The patient was assessed as Fitzpatrick skin type III. A clinical close-up photograph of a skin lesion. History notes pesticide exposure, prior skin cancer (patient or family), prior malignancy (patient or family), and no alcohol use:
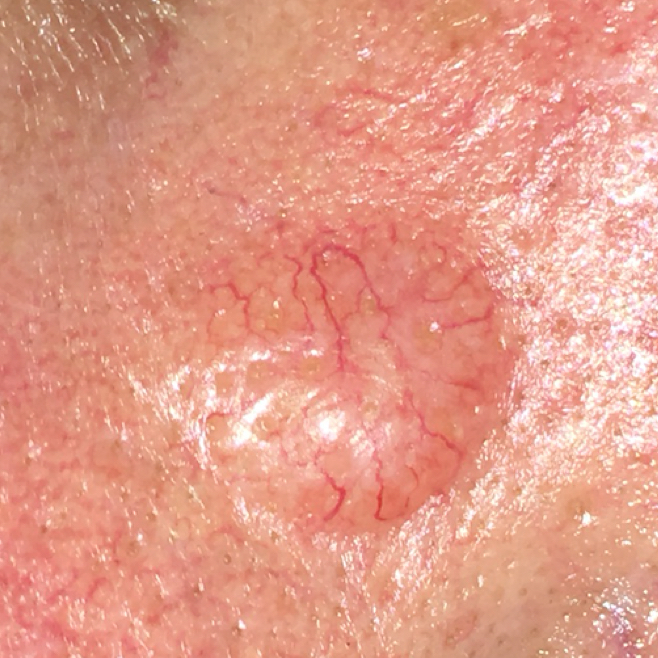Patient and lesion: The lesion is located on the nose. Measuring about 11 × 9 mm. The patient reports that the lesion is elevated, has grown, has changed, and itches. Diagnosis: Confirmed on histopathology as a basal cell carcinoma.